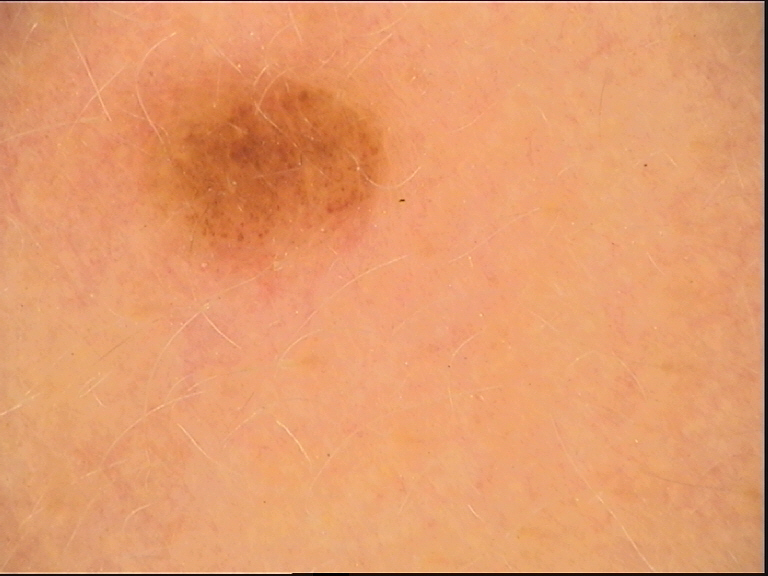Labeled as a benign lesion — a dysplastic compound nevus.